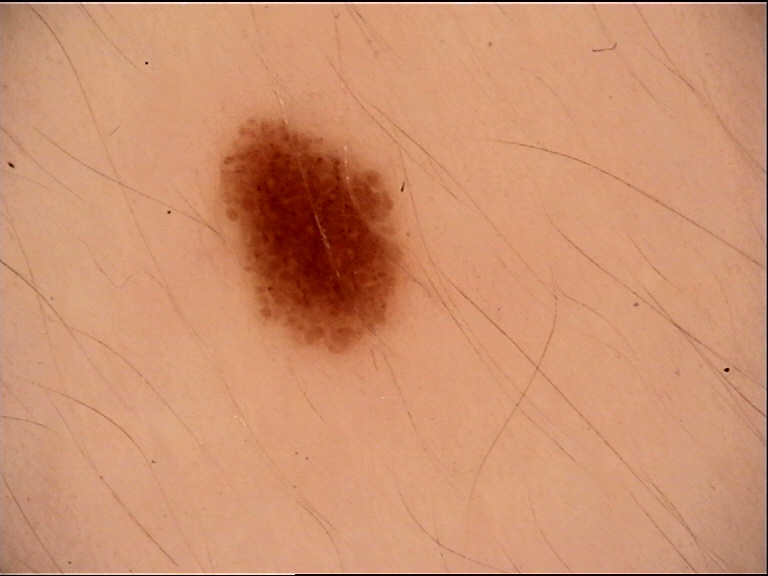Case:
A skin lesion imaged with a dermatoscope.
Impression:
Labeled as a benign lesion — a dysplastic junctional nevus.